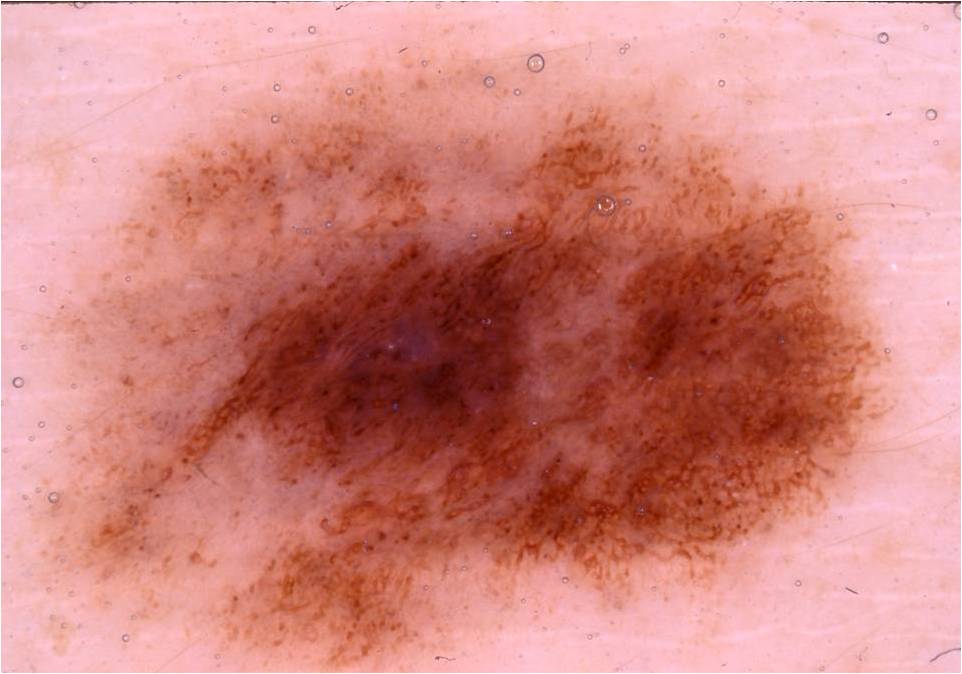Findings:
A dermoscopic close-up of a skin lesion. In (x1, y1, x2, y2) order, the lesion is located at [37, 19, 914, 672]. A large lesion occupying much of the field.
Assessment:
Diagnosed as a benign lesion.